The affected area is the head or neck · close-up view.
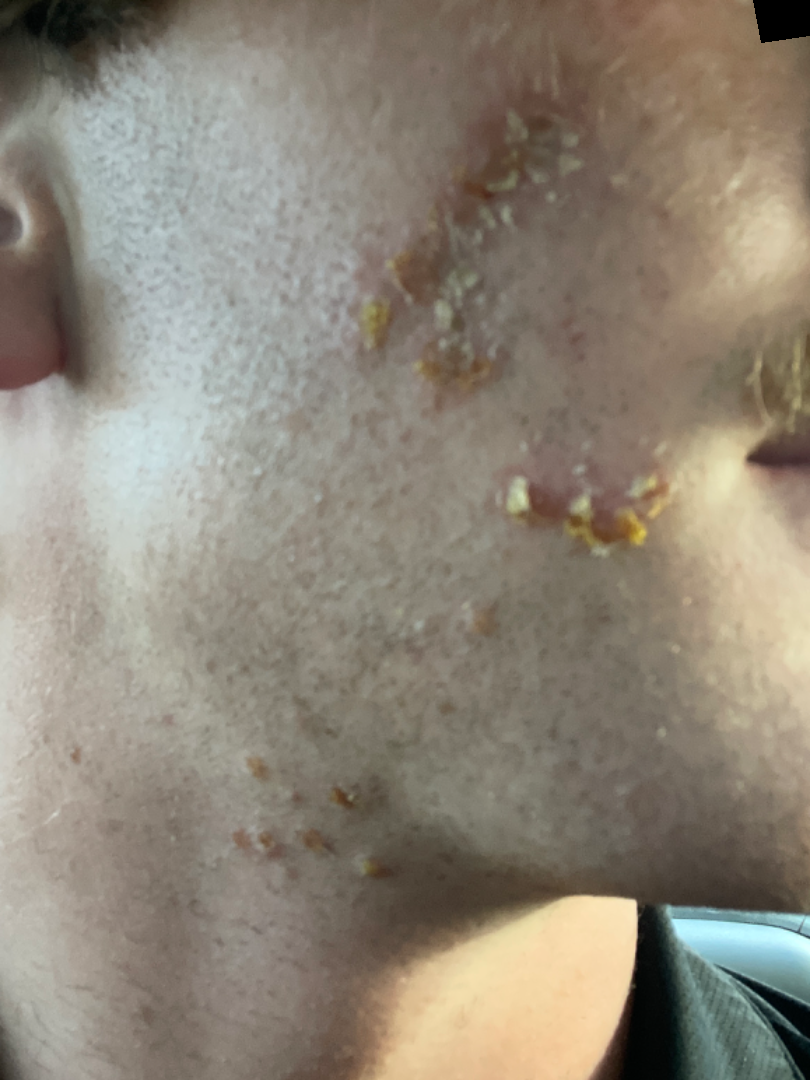The reviewing clinician's impression was: the leading consideration is Impetigo.